No constitutional symptoms were reported; the patient notes the lesion is raised or bumpy; the arm and leg are involved; reported duration is three to twelve months; female subject, age 40–49; the lesion is associated with itching, burning and enlargement; the photo was captured at a distance — 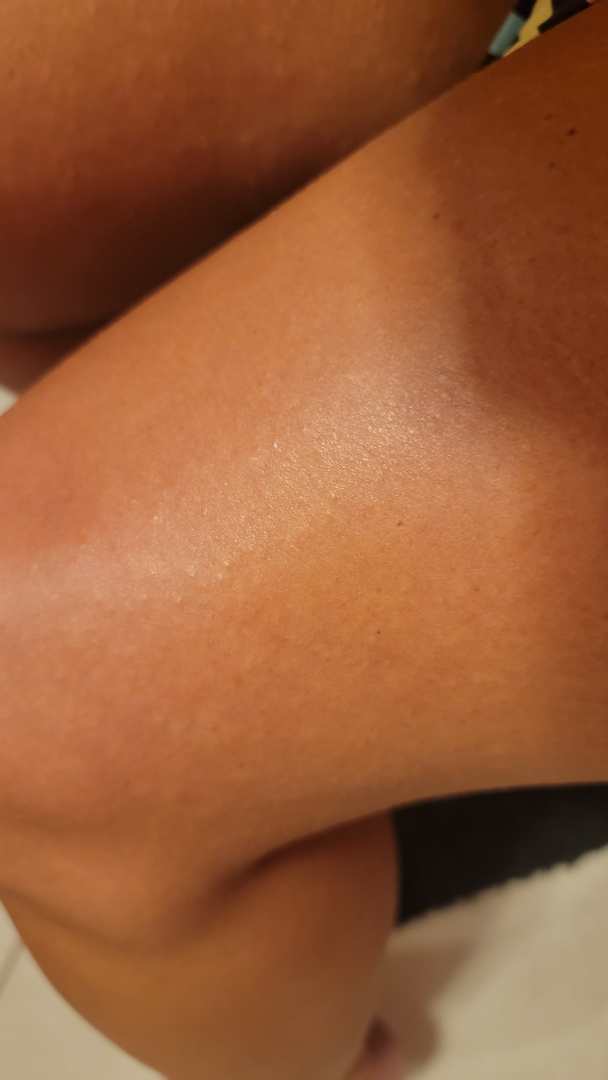| key | value |
|---|---|
| assessment | no skin condition identified |